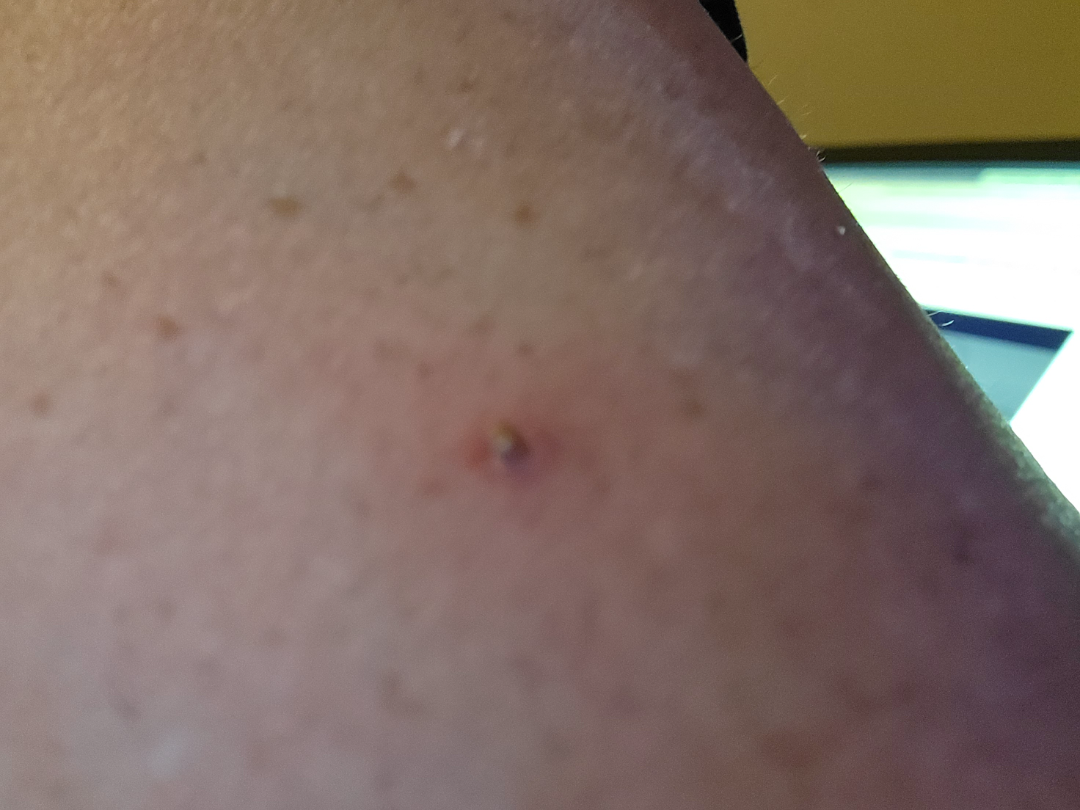Findings:
The case was indeterminate on photographic review.
Background:
Located on the leg, arm, back of the hand and top or side of the foot. The photo was captured at an angle. Female contributor, age 50–59.